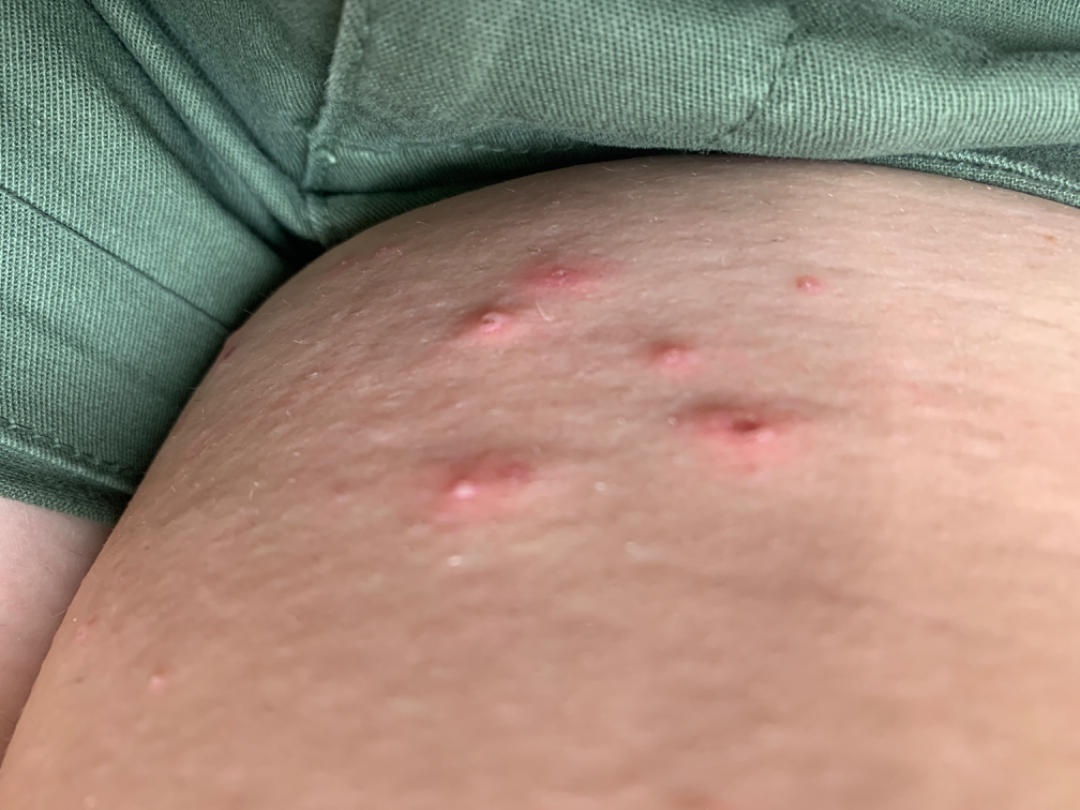The contributor is a female aged 18–29.
An image taken at an angle.
The leg is involved.
The reviewing clinician's impression was: Folliculitis (most likely).